Contact-polarized dermoscopy of a skin lesion · a male patient aged 58-62 — 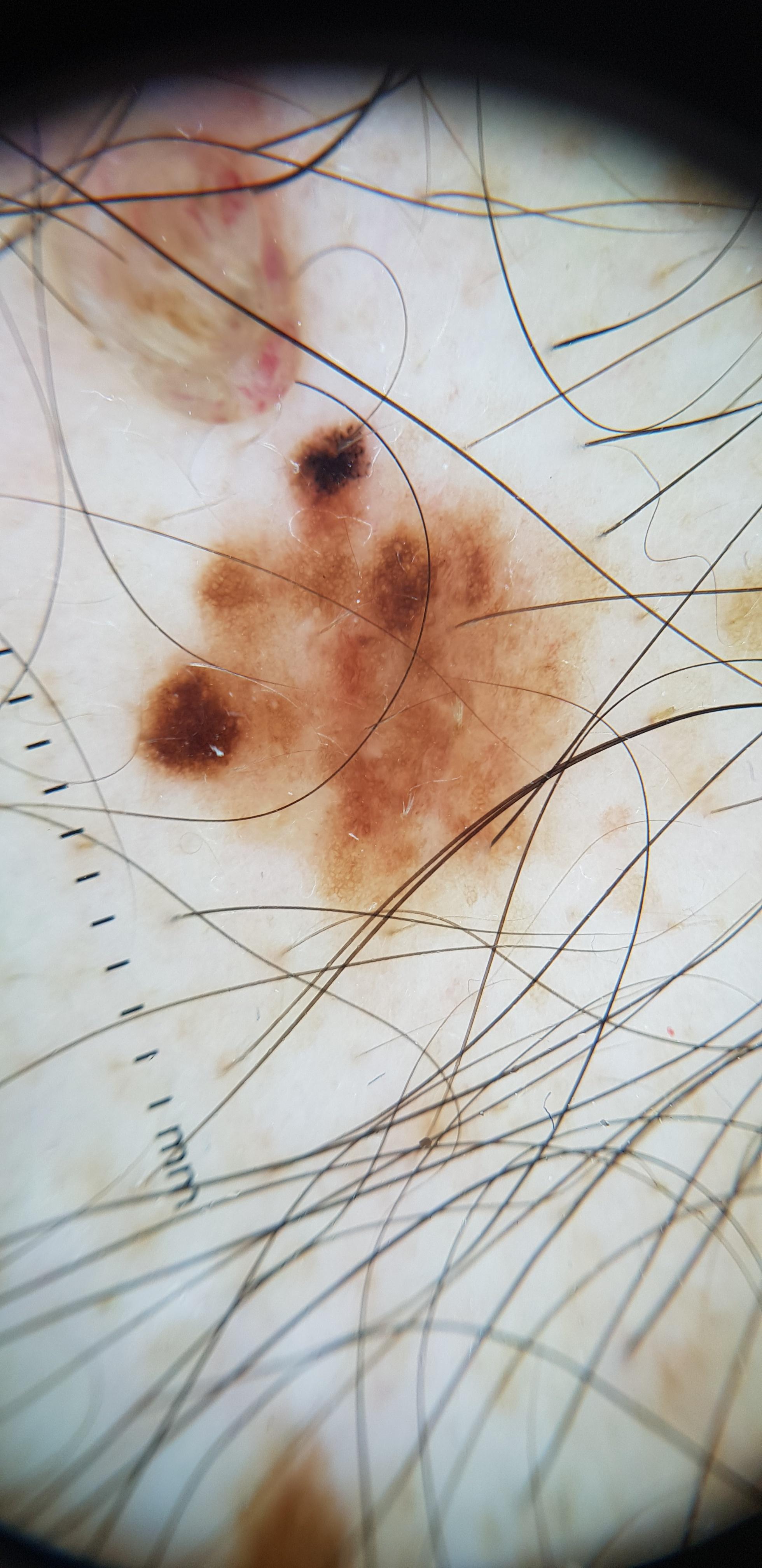Notes:
* diagnosis — Melanoma (biopsy-proven)